A close-up photograph. The lesion is described as raised or bumpy. The condition has been present for about one day. The top or side of the foot is involved. The patient is a female aged 40–49. Symptoms reported: itching and bothersome appearance:
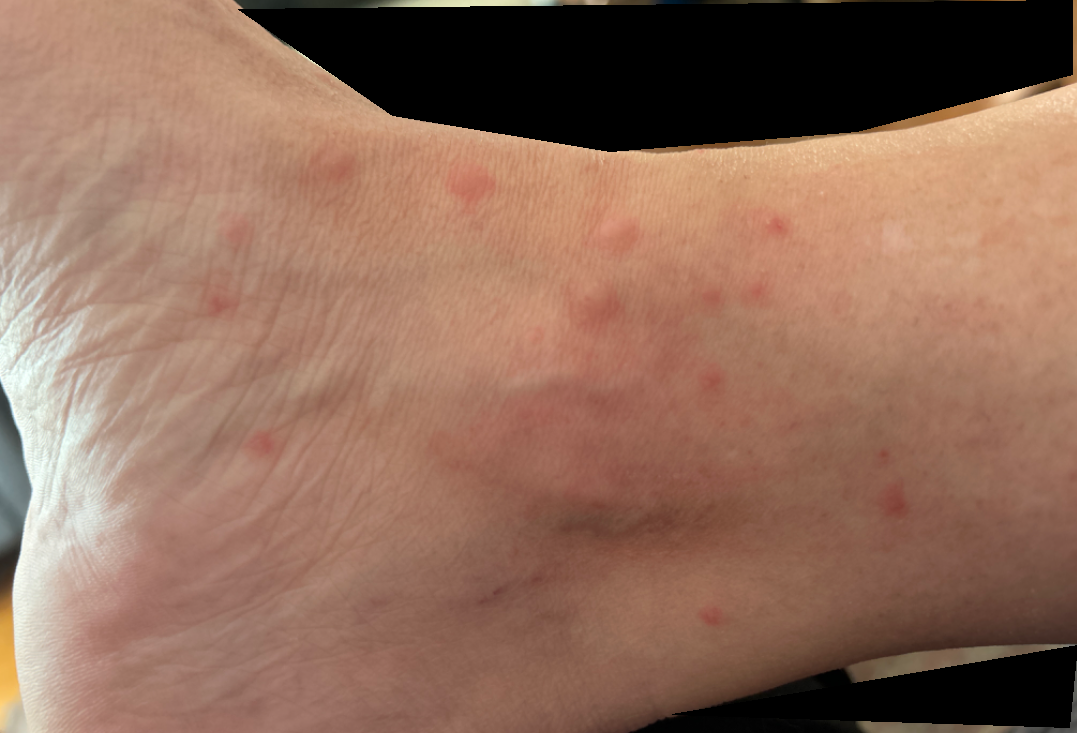assessment: unable to determine.